A skin lesion imaged with a dermatoscope.
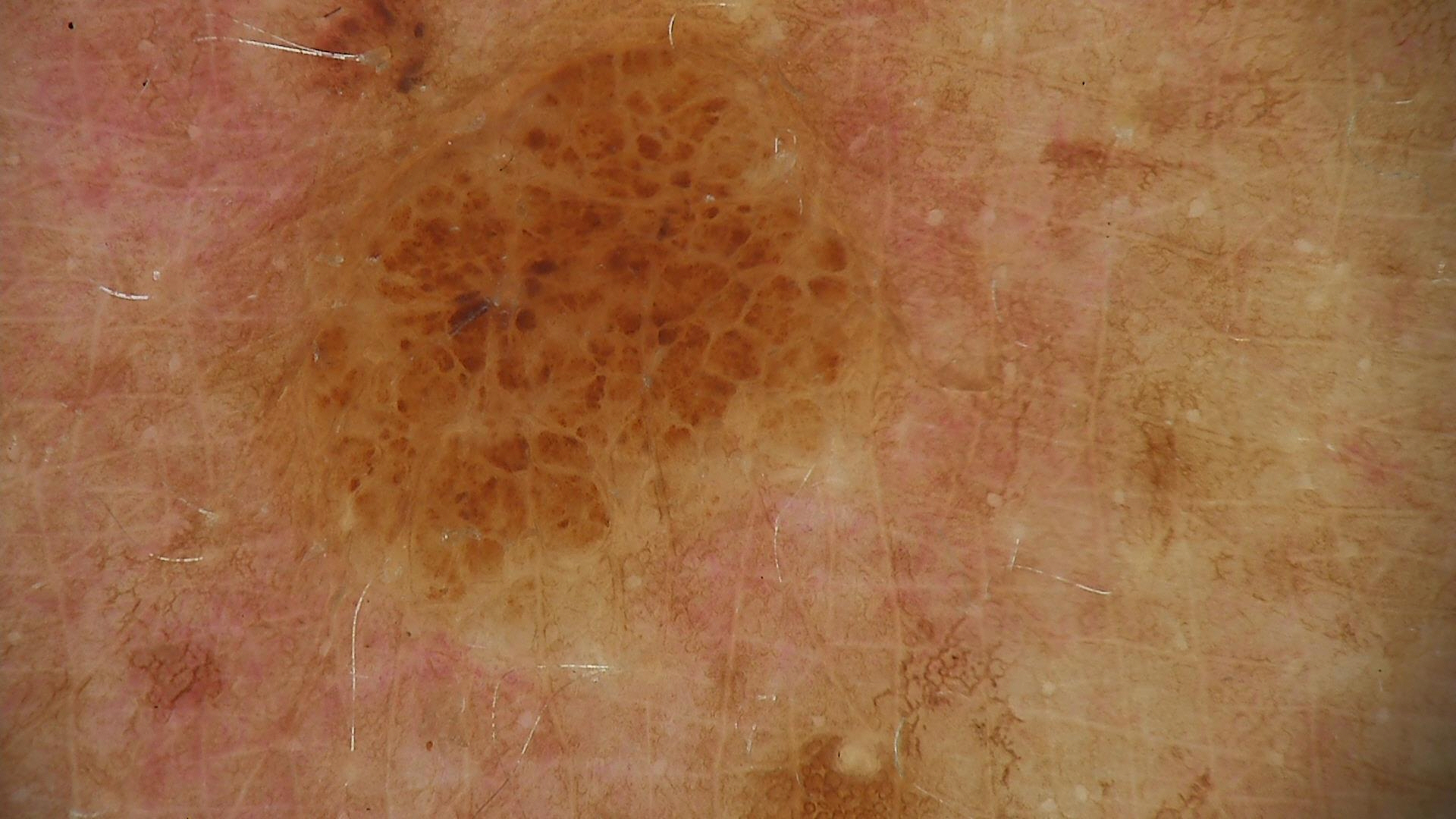classification — banal
diagnostic label — compound nevus (expert consensus)